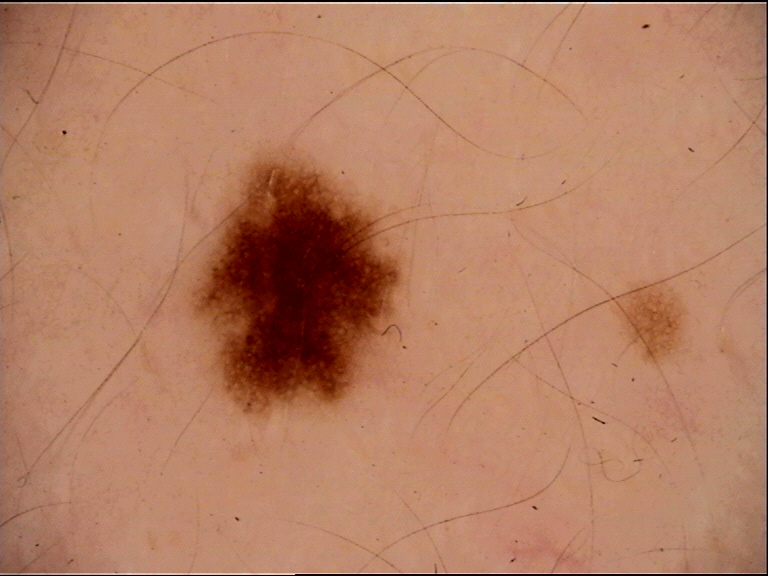modality: dermatoscopy
diagnosis: dysplastic junctional nevus (expert consensus)